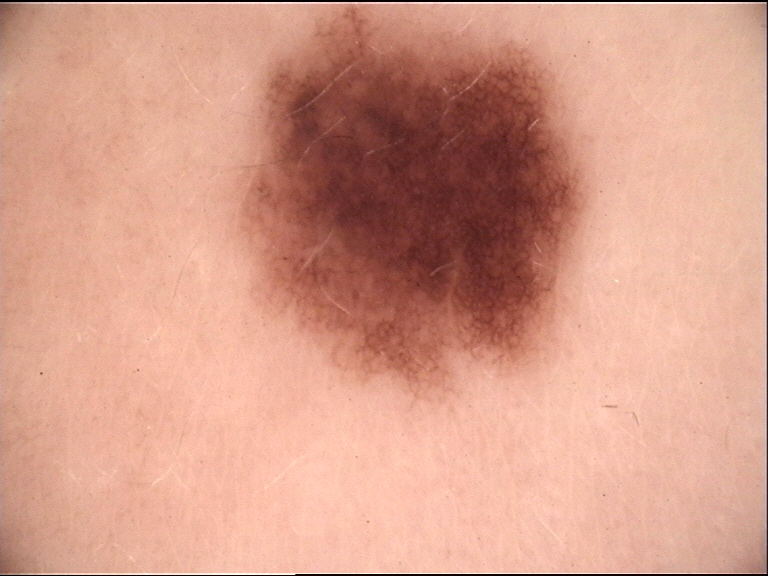Case:
A dermatoscopic image of a skin lesion.
Impression:
Classified as a dysplastic junctional nevus.